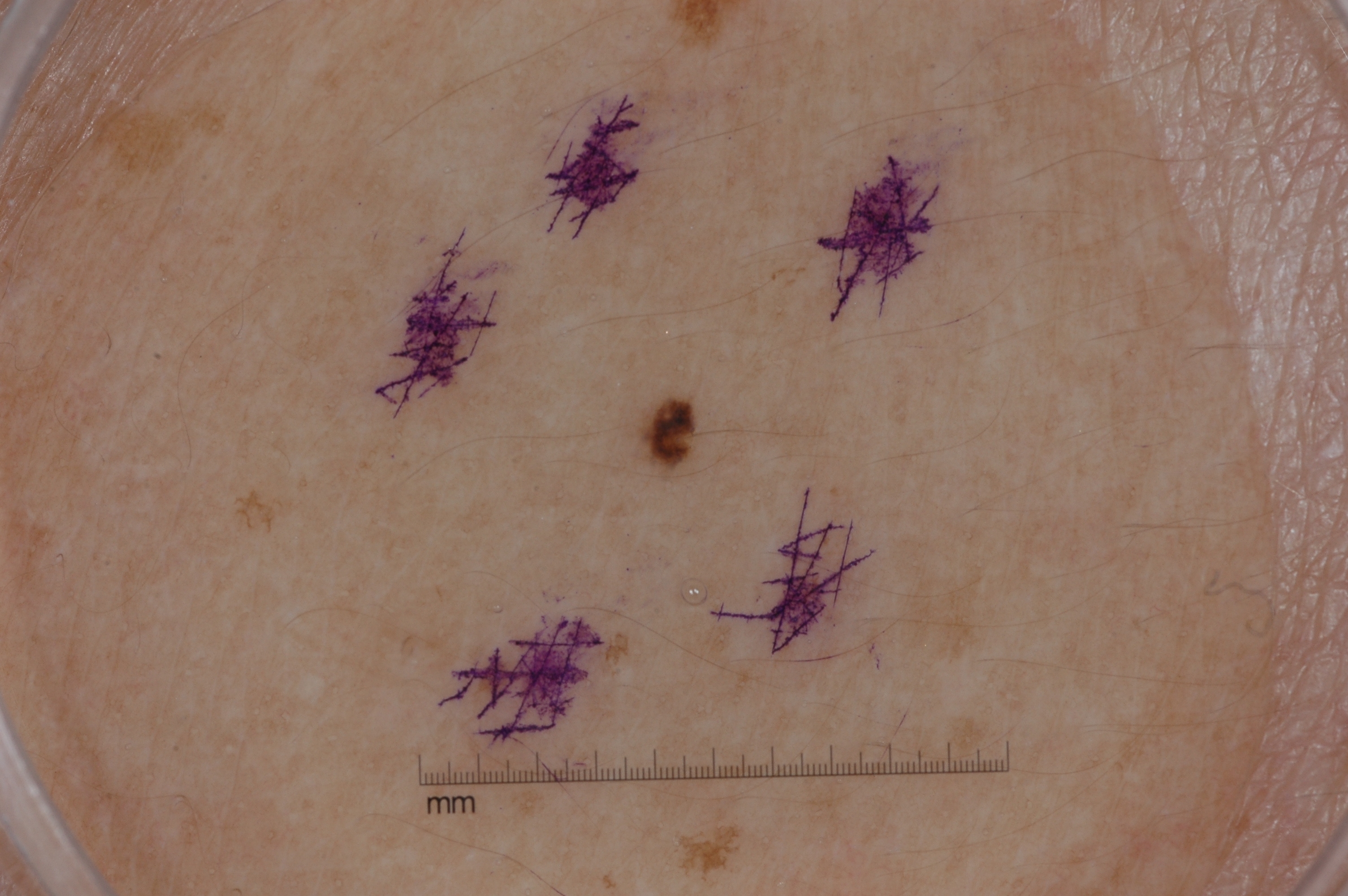Q: How was this image acquired?
A: dermoscopy of a skin lesion
Q: Patient demographics?
A: female, approximately 35 years of age
Q: What dermoscopic features are not present?
A: streaks, milia-like cysts, negative network, and pigment network
Q: Lesion extent?
A: small
Q: Where is the lesion located?
A: <box>639, 395, 701, 470</box>
Q: What did the assessment conclude?
A: a melanocytic nevus, a benign lesion